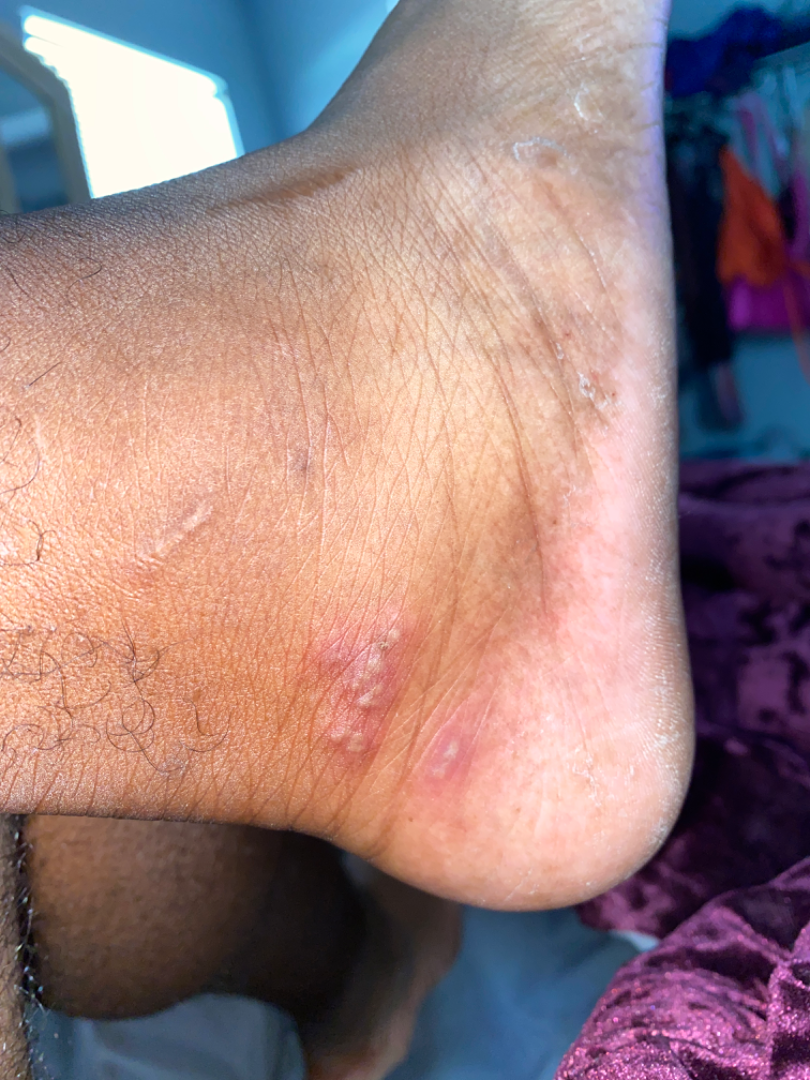Case summary:
– assessment: unable to determine
– view: at a distance
– site: sole of the foot